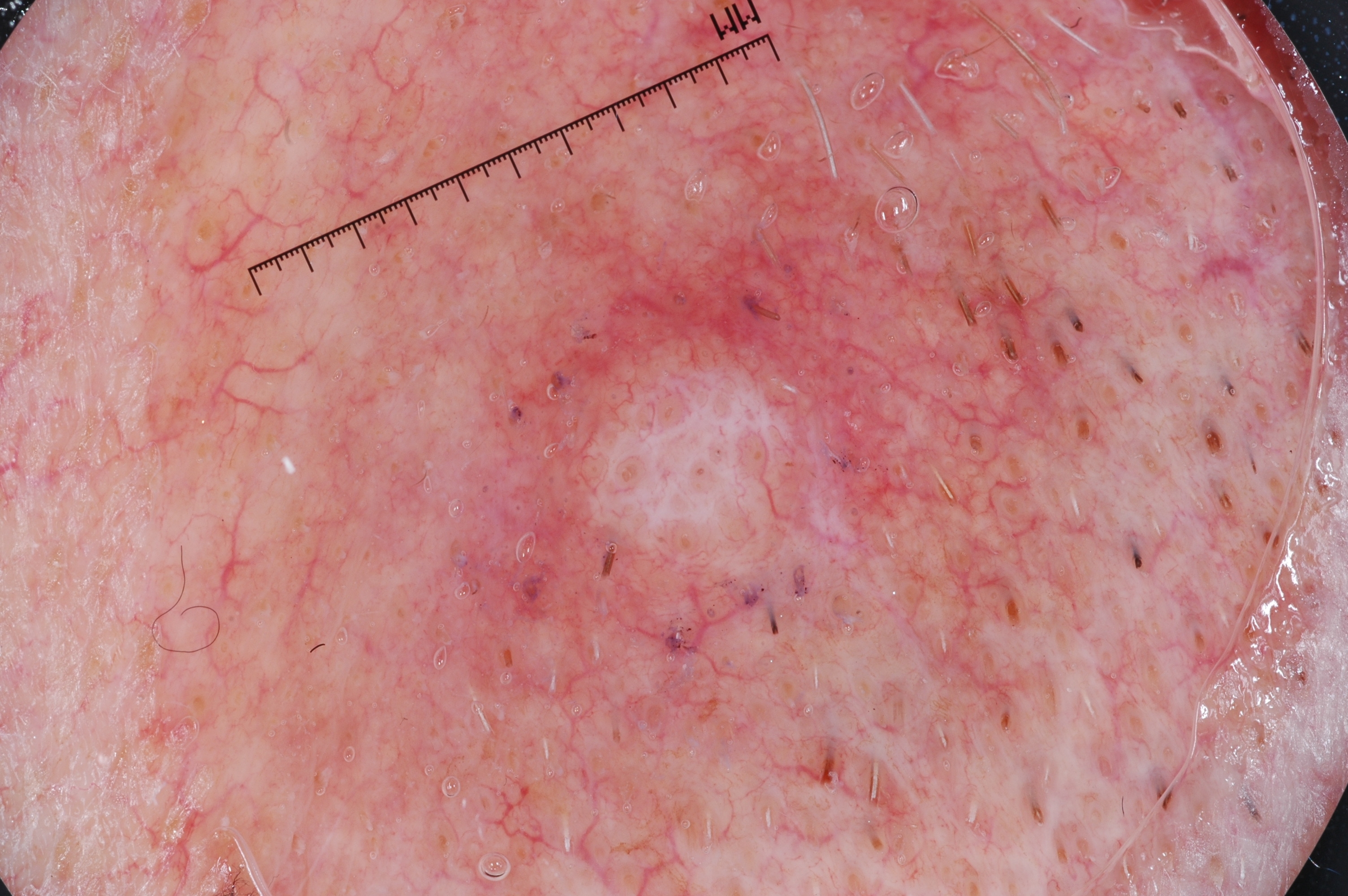modality=dermoscopy of a skin lesion
bounding box=(410, 182, 933, 773)
dermoscopic findings=negative network
diagnostic label=a melanocytic nevus